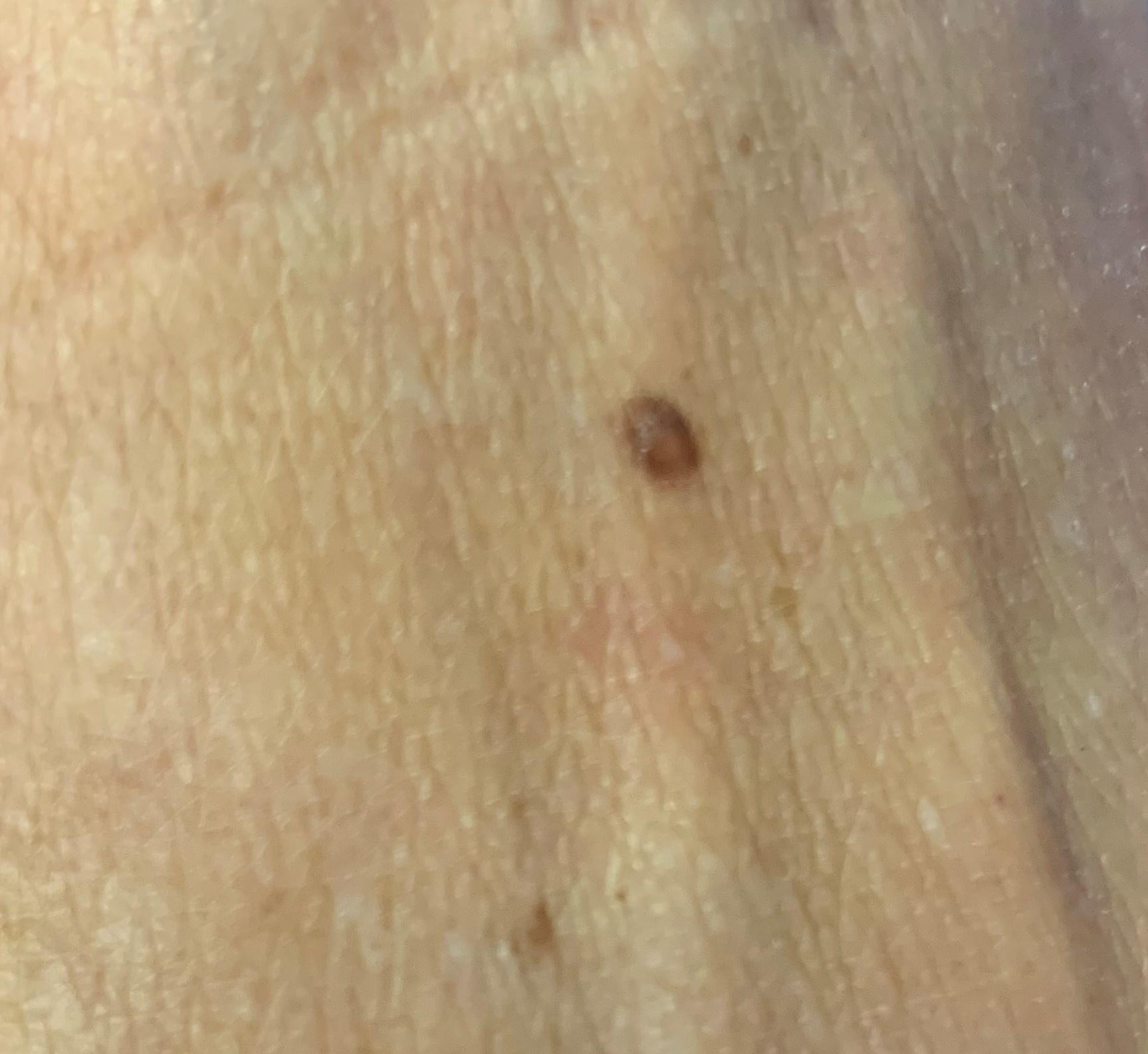{
  "image": "clinical photo (overview)",
  "patient": {
    "age_approx": 45,
    "sex": "female"
  },
  "diagnosis": {
    "name": "Nevus",
    "malignancy": "benign",
    "confirmation": "histopathology",
    "lineage": "melanocytic"
  }
}